A dermoscopic image of a skin lesion:
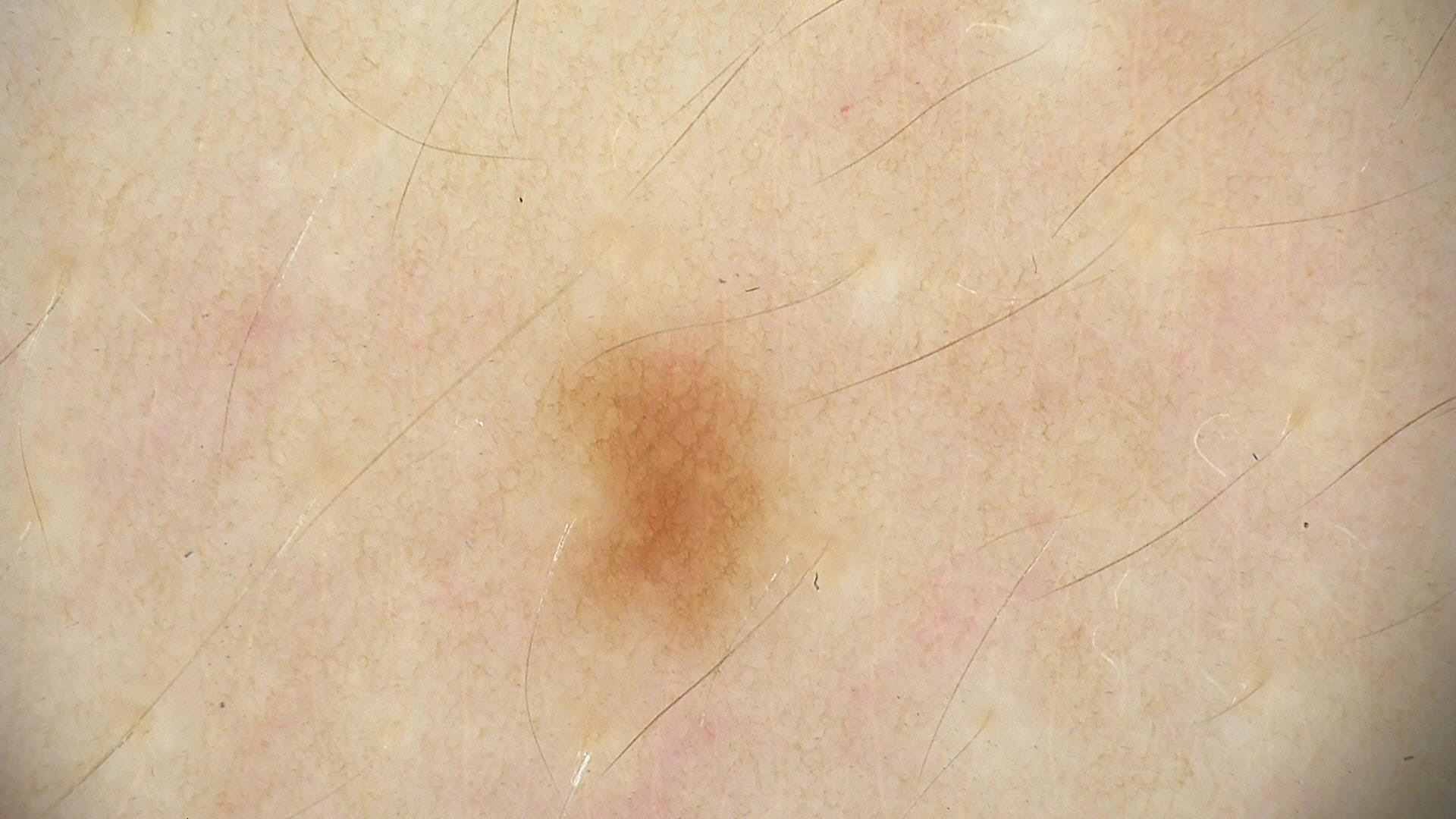diagnostic label — dysplastic junctional nevus (expert consensus).